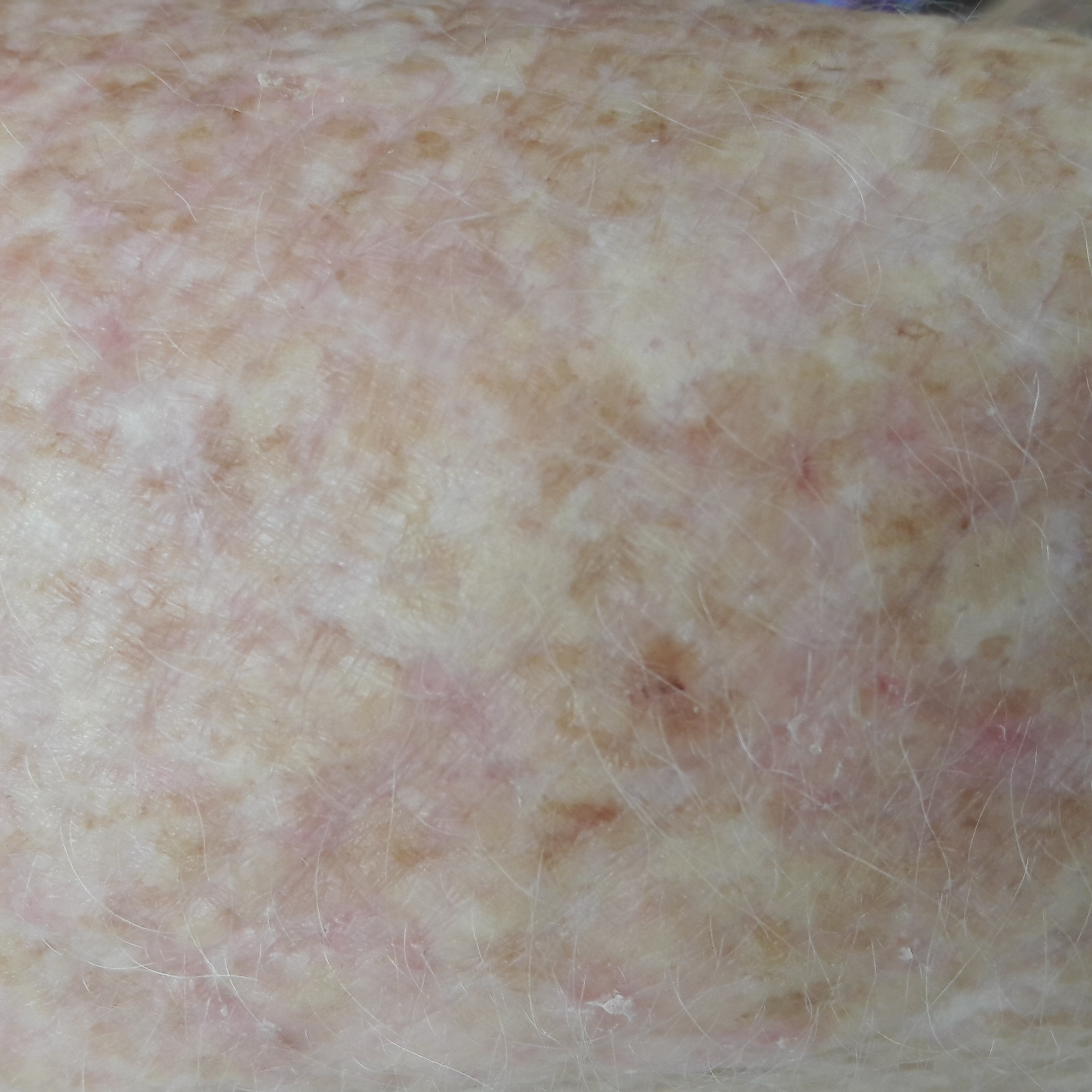Notes:
- subject — 67 years of age
- anatomic site — a forearm
- reported symptoms — itching
- impression — actinic keratosis (clinical consensus)